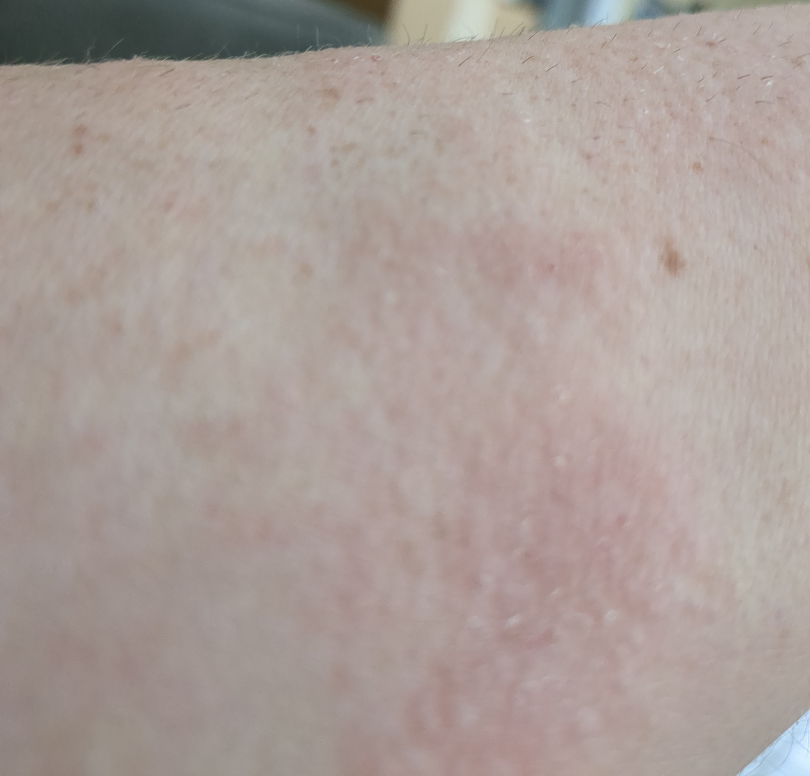Patient information: This image was taken at an angle. The affected area is the arm. The contributor is male. The patient indicates the lesion is raised or bumpy. The patient indicates the condition has been present for one to four weeks. Review: On photographic review by a dermatologist, the leading impression is Eczema; also raised was Irritant Contact Dermatitis; less probable is Allergic Contact Dermatitis.